A dermoscopic close-up of a skin lesion: 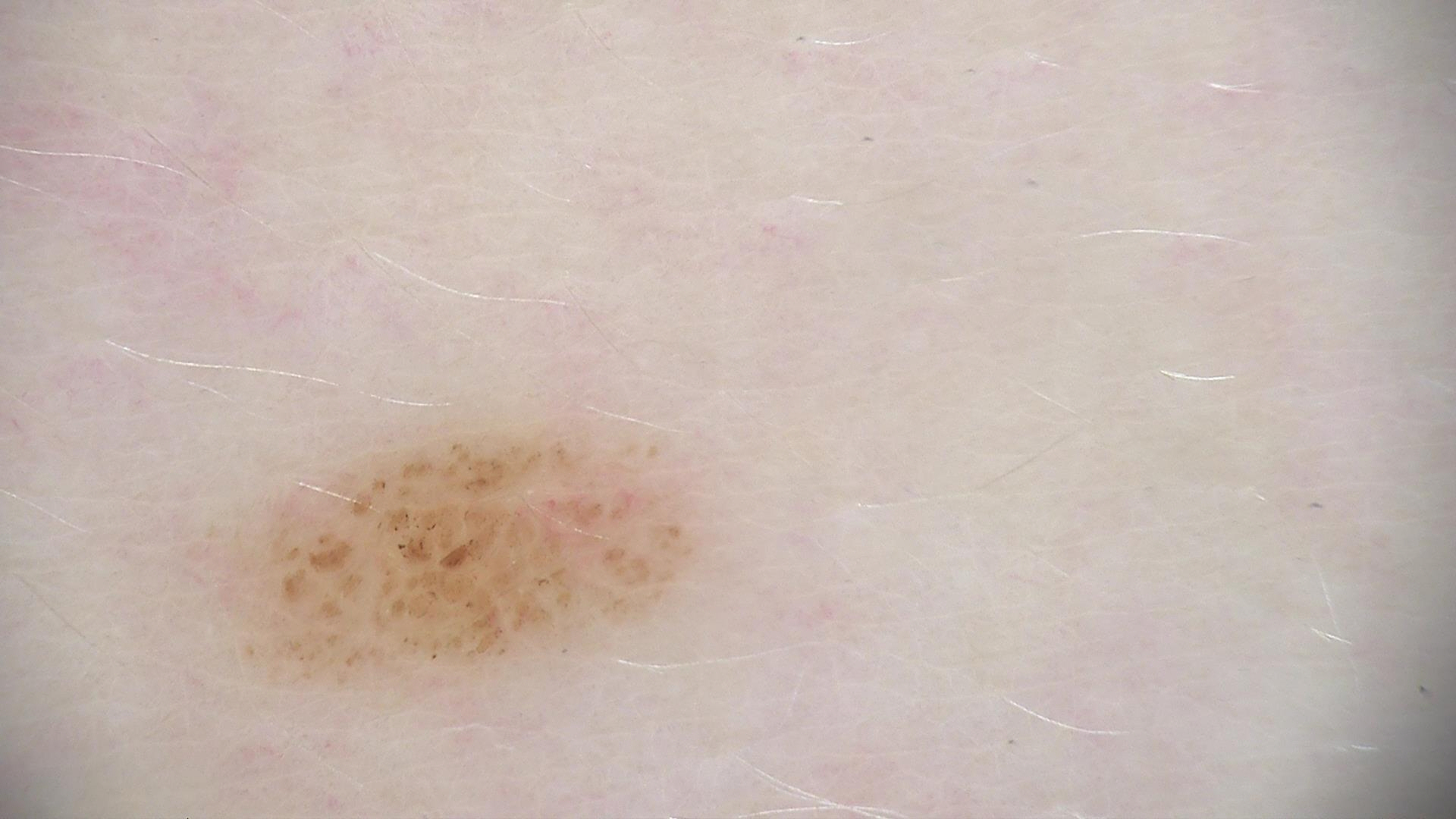Diagnosed as a compound nevus.